Dermoscopy of a skin lesion.
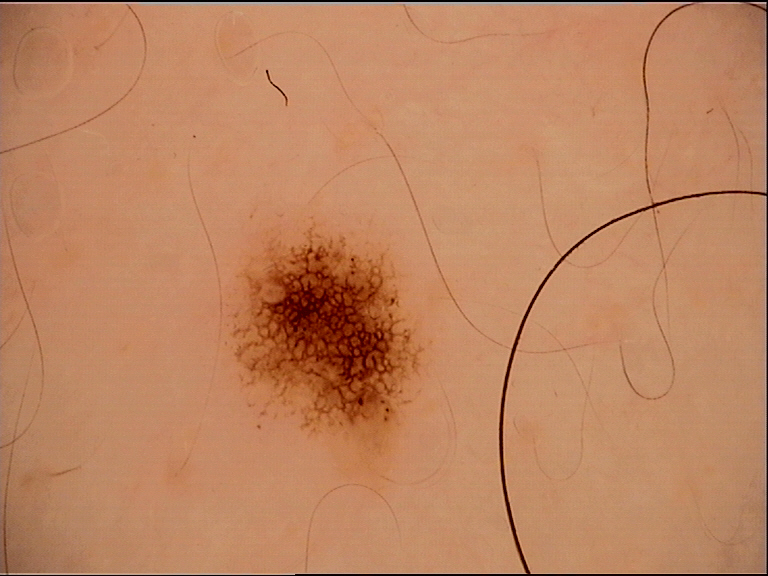Q: What was the diagnostic impression?
A: dysplastic junctional nevus (expert consensus)